A dermoscopic view of a skin lesion:
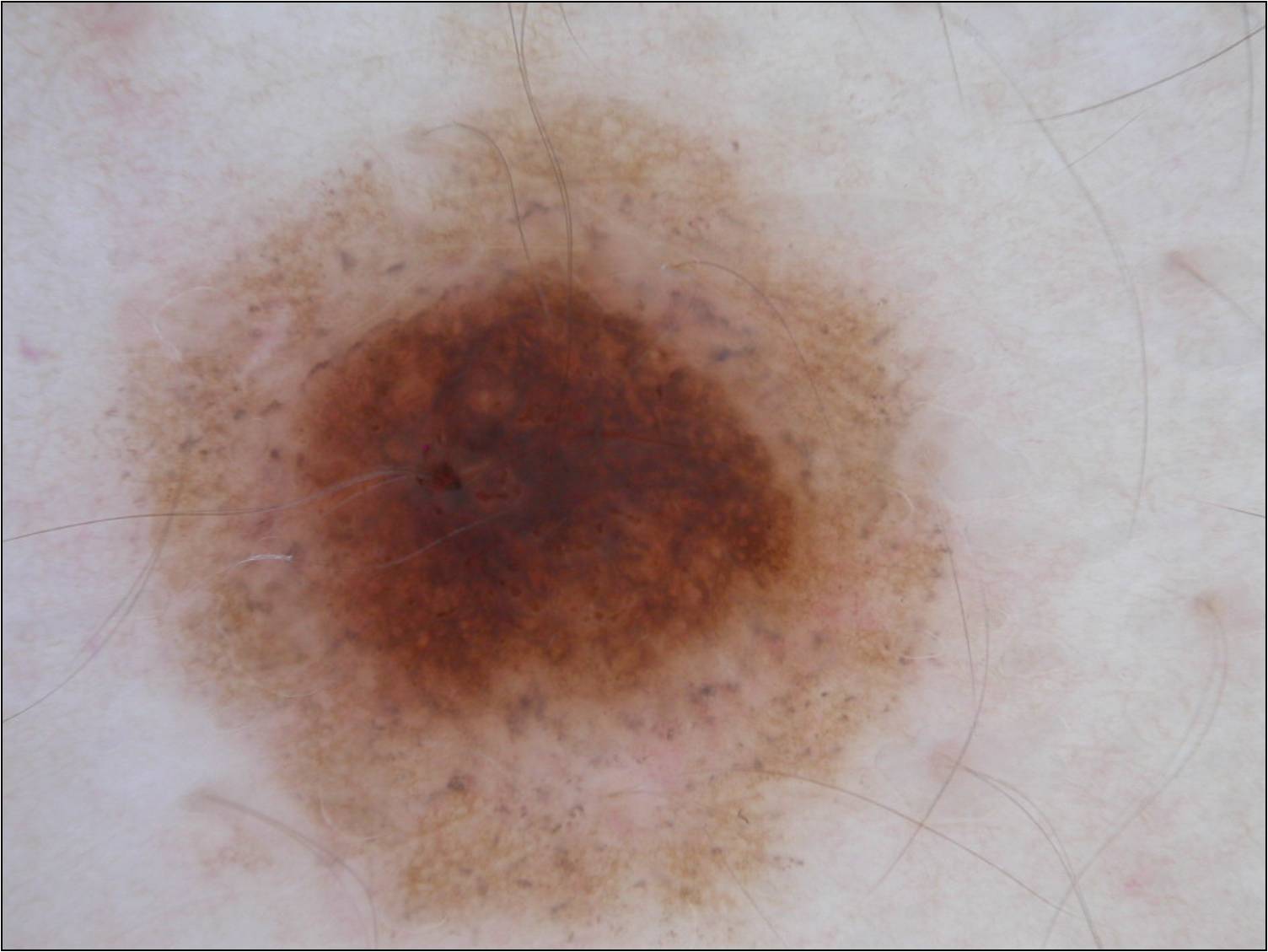The lesion's extent is [94,79,970,942].
Consistent with a benign lesion.